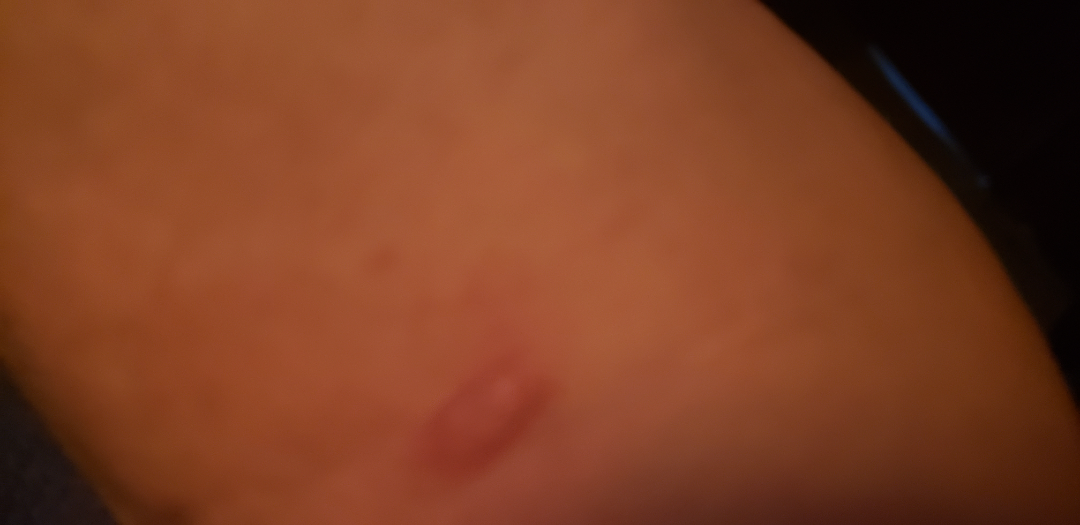Q: What was the assessment?
A: unable to determine
Q: Anatomic location?
A: arm
Q: Who is the patient?
A: male, age 50–59
Q: What is the framing?
A: at an angle